A female patient age 75; a clinical photograph of a skin lesion.
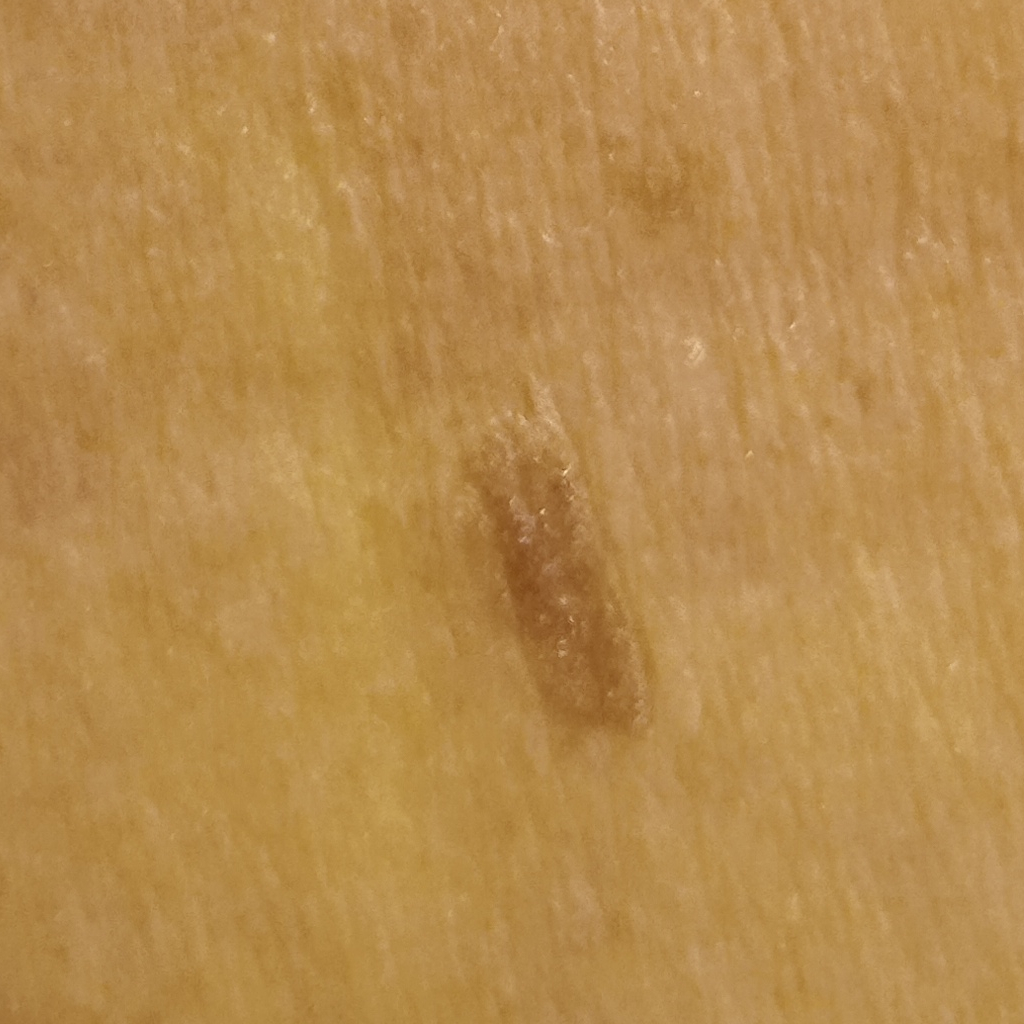Q: Where is the lesion?
A: the back
Q: Lesion size?
A: 8.4 mm
Q: What was the diagnosis?
A: seborrheic keratosis (dermatologist consensus)